The photo was captured at an angle: 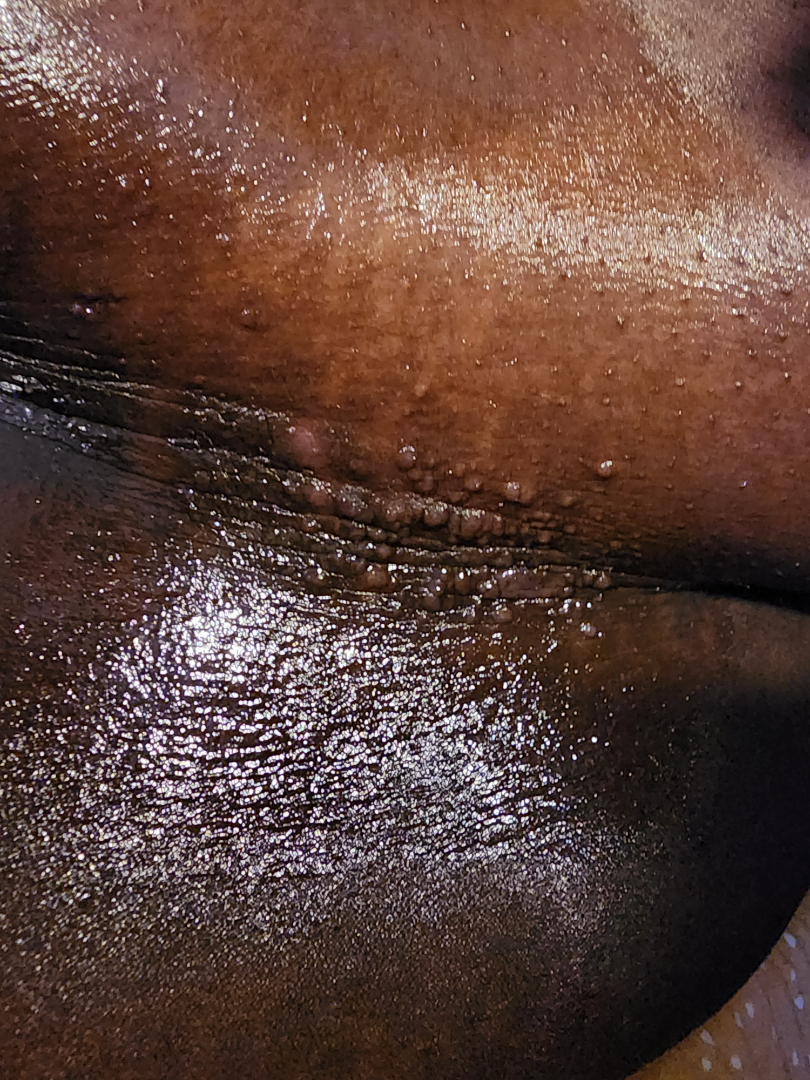{
  "assessment": "unable to determine"
}